Close-up view:
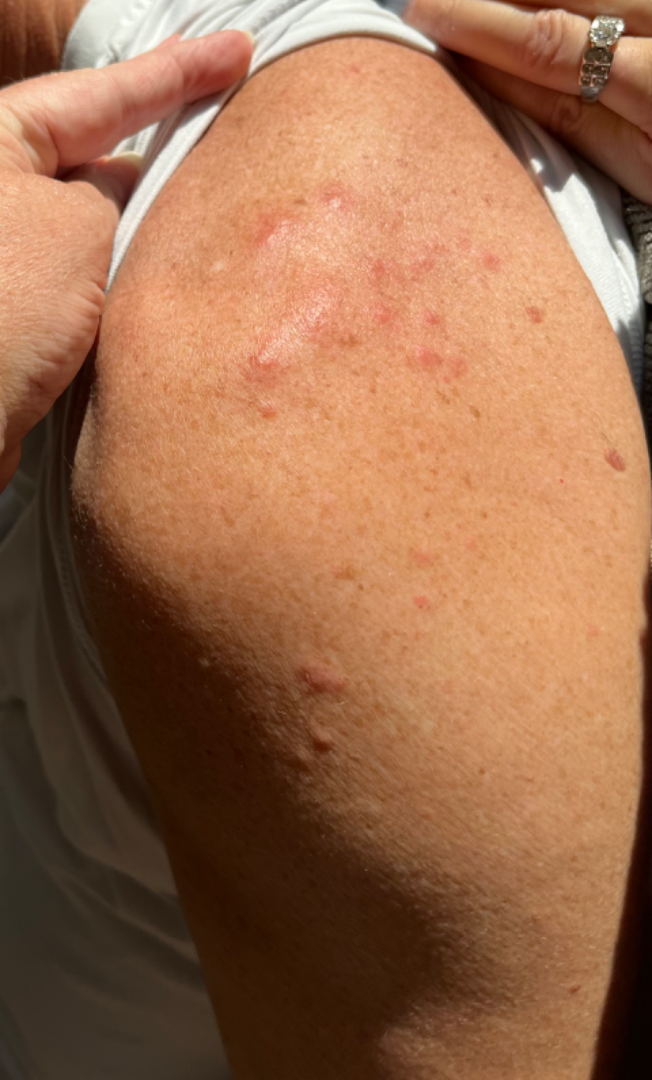differential:
  leading:
    - Folliculitis
  considered:
    - Granuloma annulare